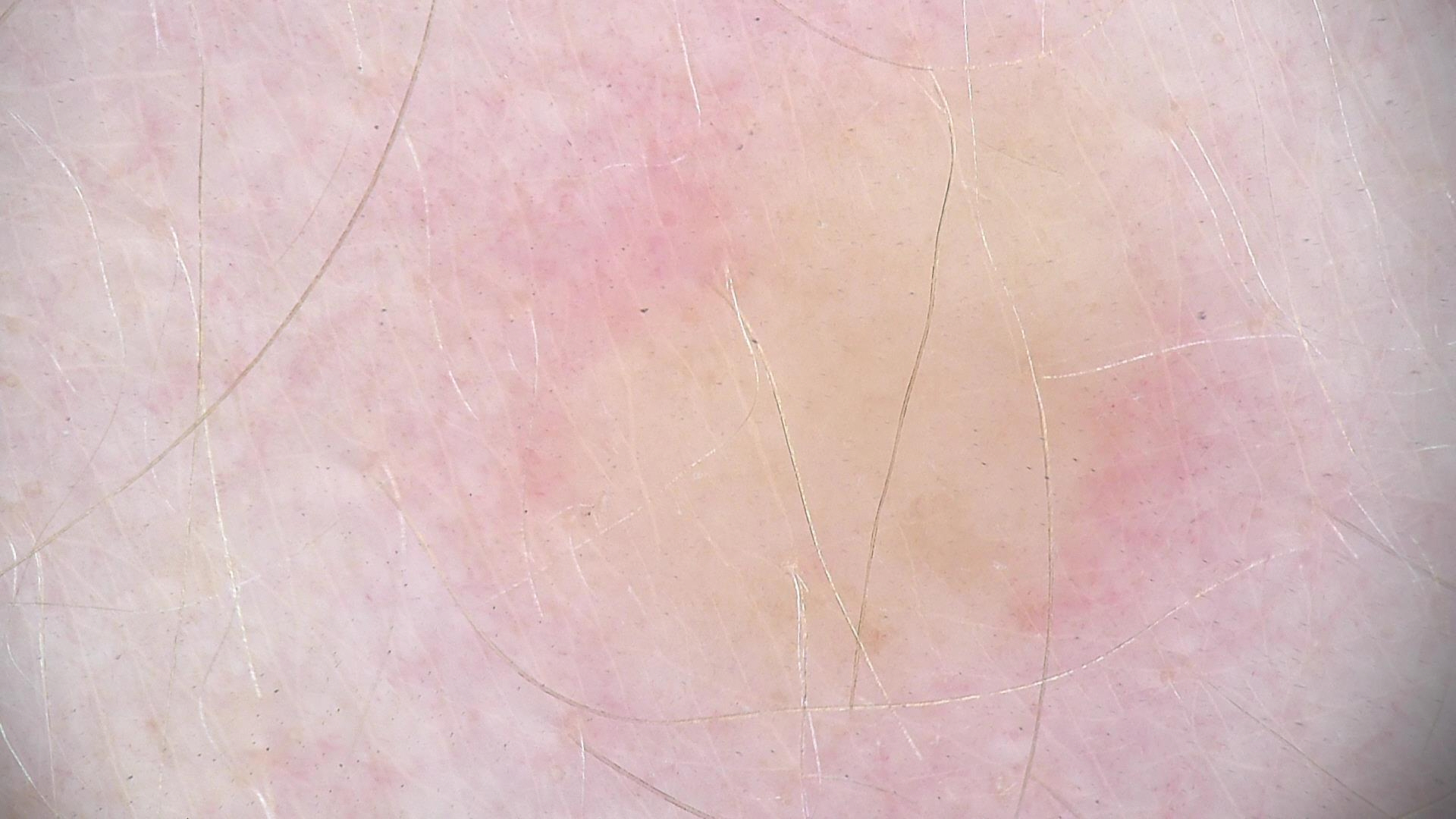Case:
– modality — dermoscopy
– classification — fibro-histiocytic
– class — dermatofibroma (expert consensus)